A dermoscopic image of a skin lesion, the patient is a male in their mid- to late 30s: 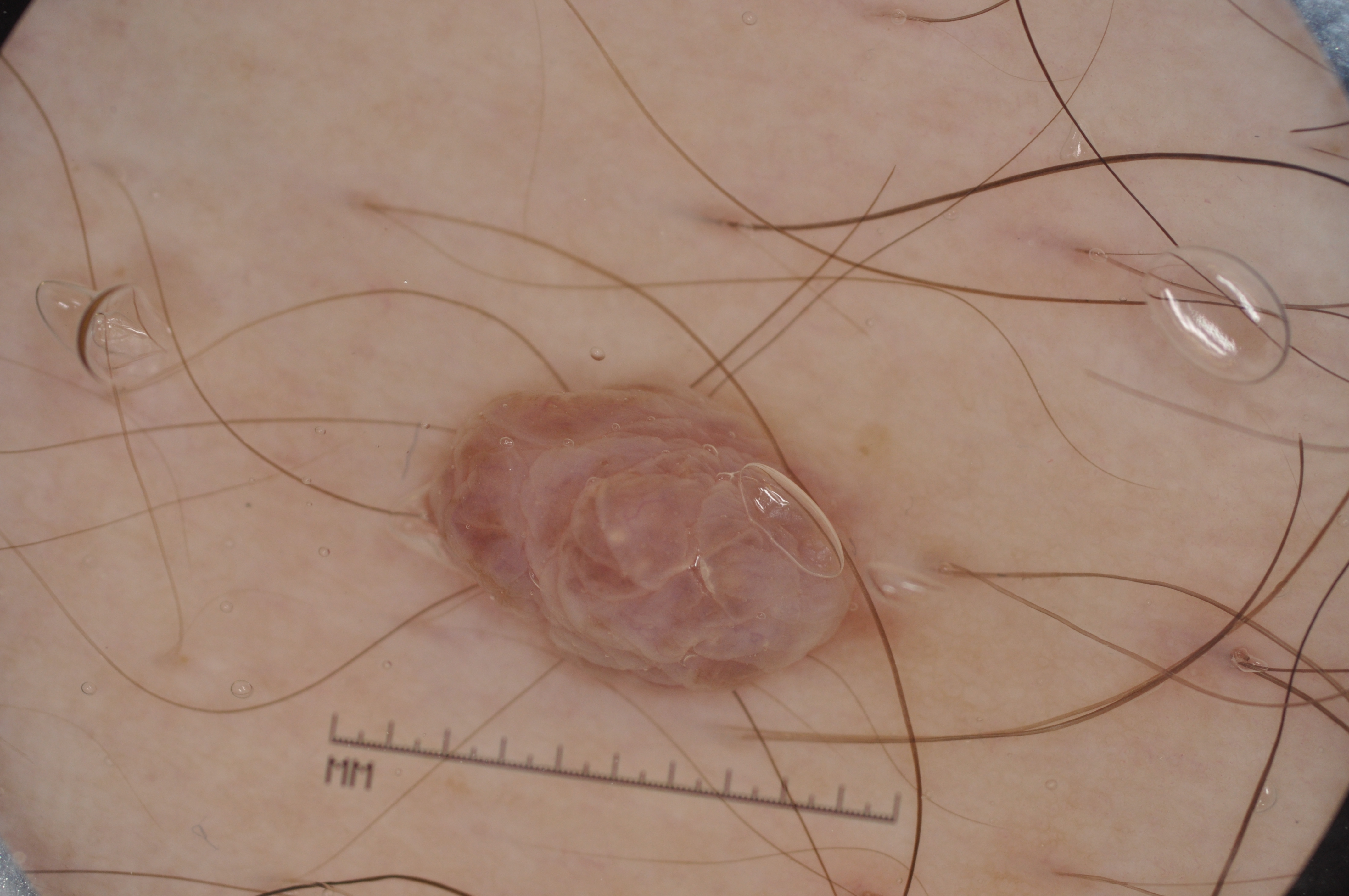bounding box: <box>422, 365, 885, 700</box>; dermoscopic findings: milia-like cysts; extent: ~10% of the field; impression: a melanocytic nevus.